Reported lesion symptoms include bothersome appearance · the contributor reports the lesion is raised or bumpy · the photograph was taken at an angle · the arm is involved · human graders estimated a MST of 2 · the condition has been present for one to four weeks · the patient is 18–29, male · the patient considered this a rash.
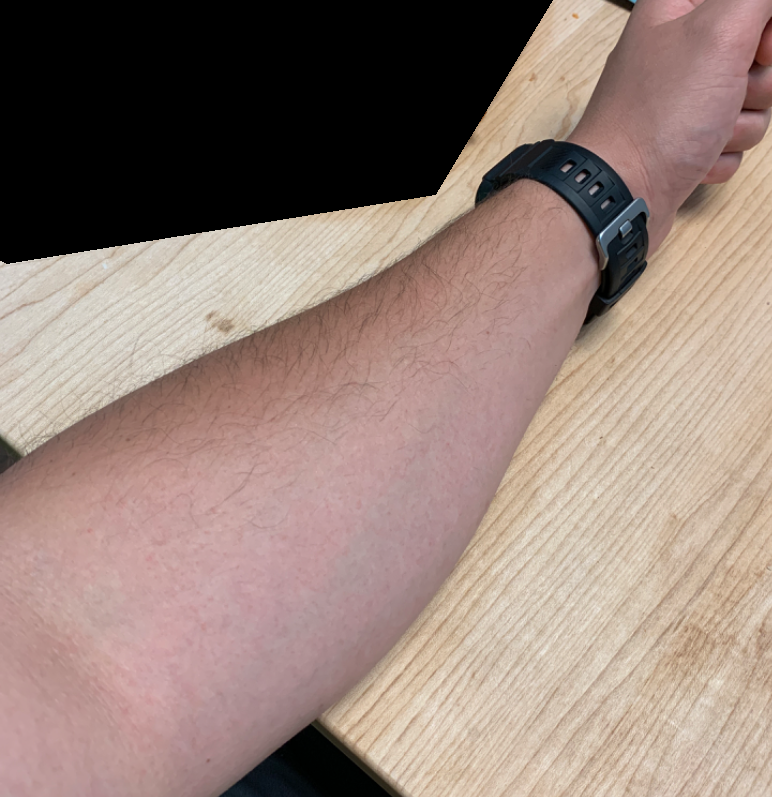Findings:
On independent review by the dermatologists, most consistent with Eczema; also consider Keratosis pilaris.